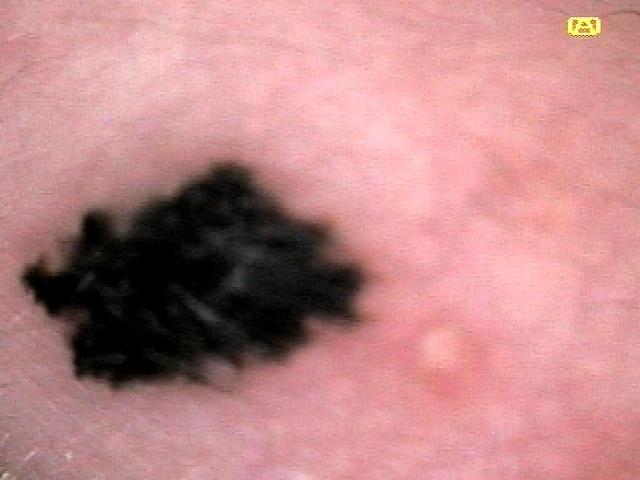Q: Patient demographics?
A: male, aged around 40
Q: Where on the body is the lesion?
A: the trunk, specifically the lateral trunk
Q: What is this lesion?
A: Melanoma (biopsy-proven)